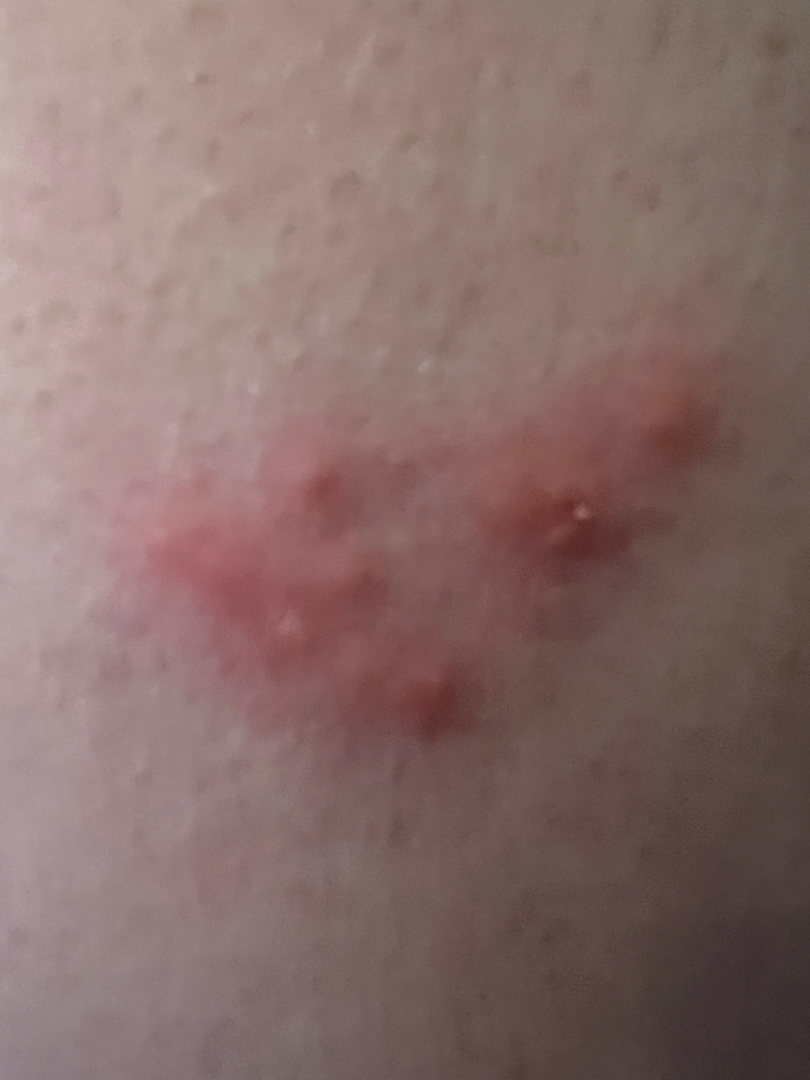{"duration": "about one day", "texture": "raised or bumpy", "patient_category": "a rash", "symptoms": ["bothersome appearance", "itching"], "body_site": "front of the torso", "shot_type": "close-up", "patient": "male, age 50–59", "differential": {"leading": ["Eczema"], "considered": ["Herpes Simplex"]}}